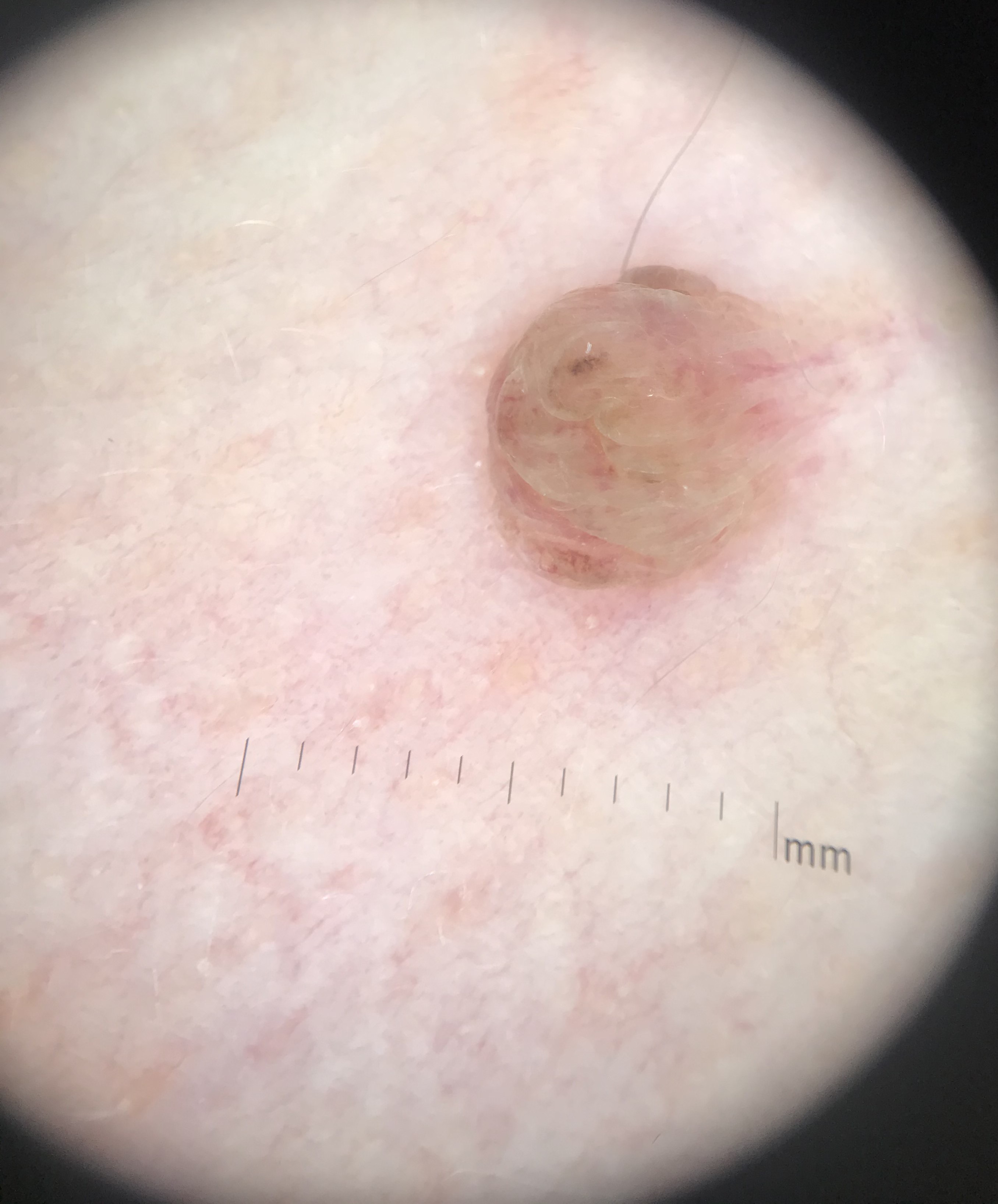Classified as a dermal nevus.